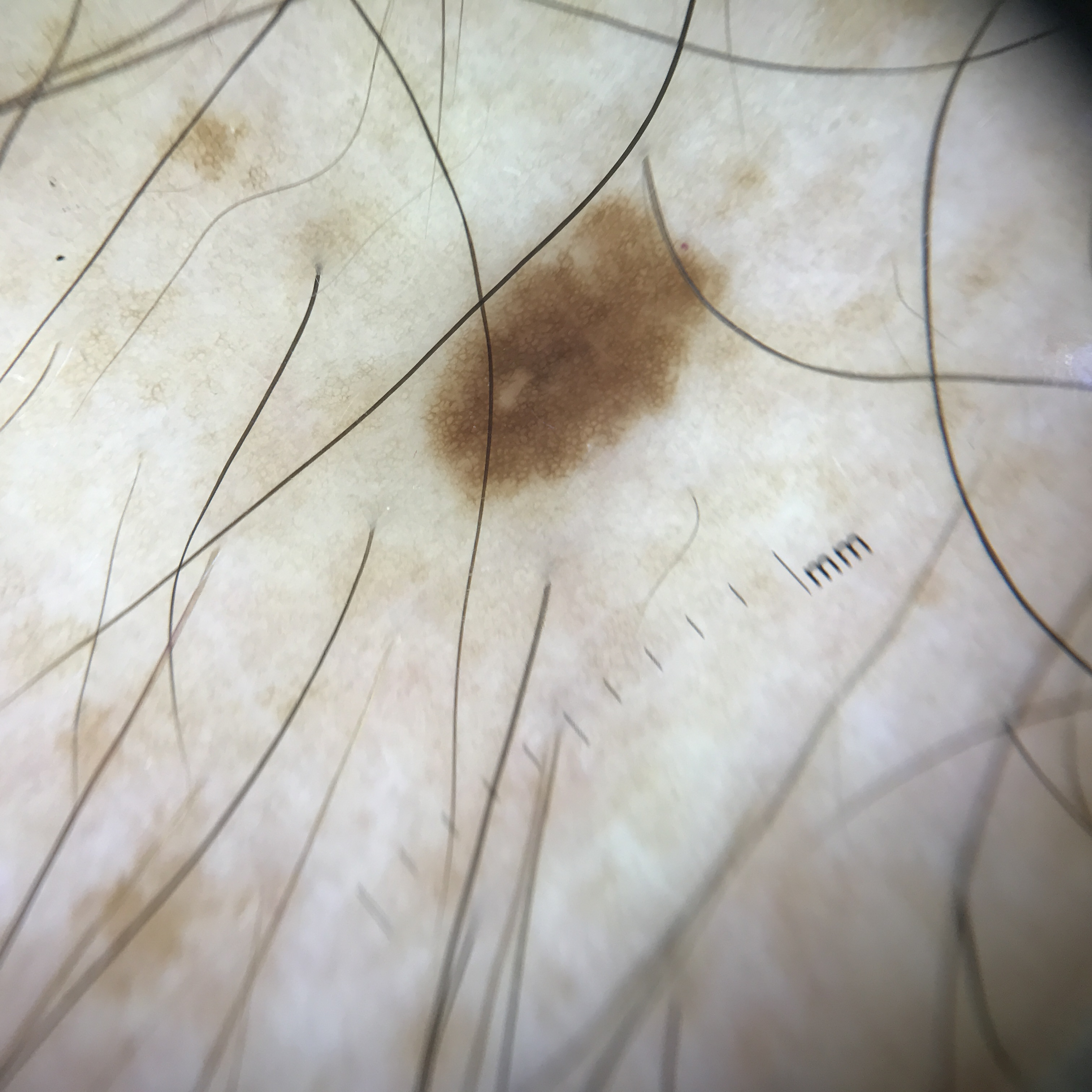<lesion>
<image>dermoscopy</image>
<lesion_type>
<main_class>banal</main_class>
<pattern>junctional</pattern>
</lesion_type>
<diagnosis>
<name>junctional nevus</name>
<code>jb</code>
<malignancy>benign</malignancy>
<super_class>melanocytic</super_class>
<confirmation>expert consensus</confirmation>
</diagnosis>
</lesion>